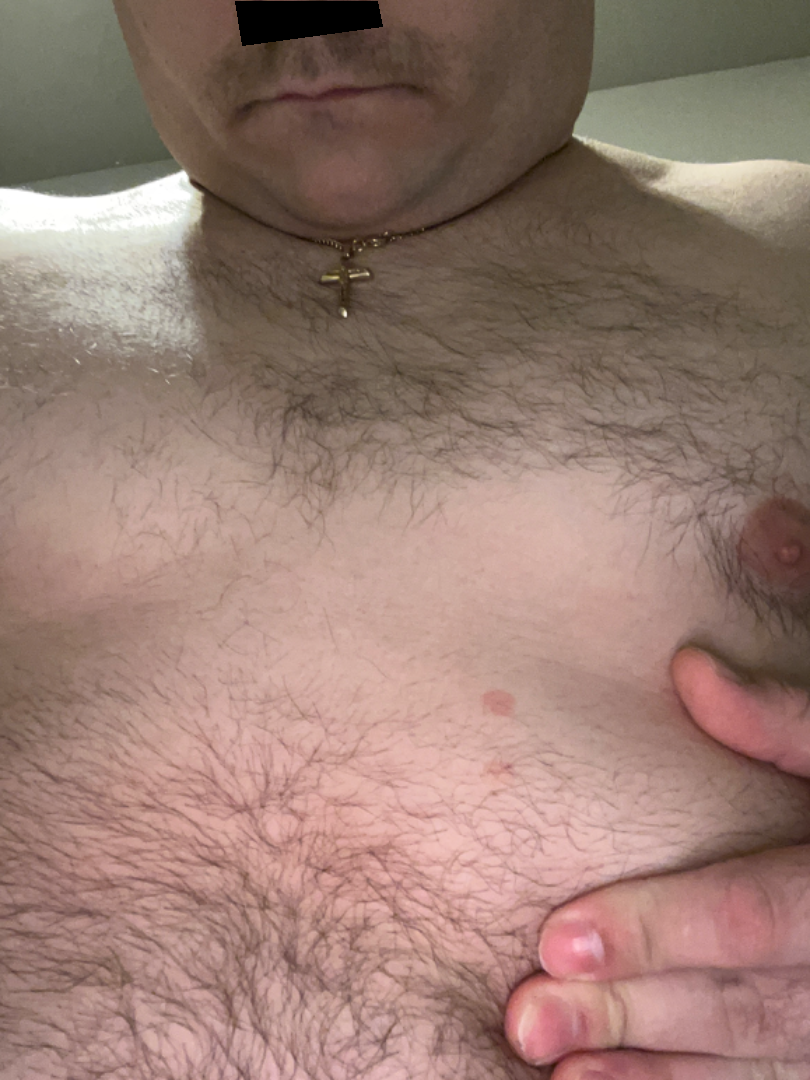Findings:
The case was difficult to assess from the available photograph.
Background:
The lesion involves the front of the torso. The photograph was taken at a distance. The subject is 18–29, male.